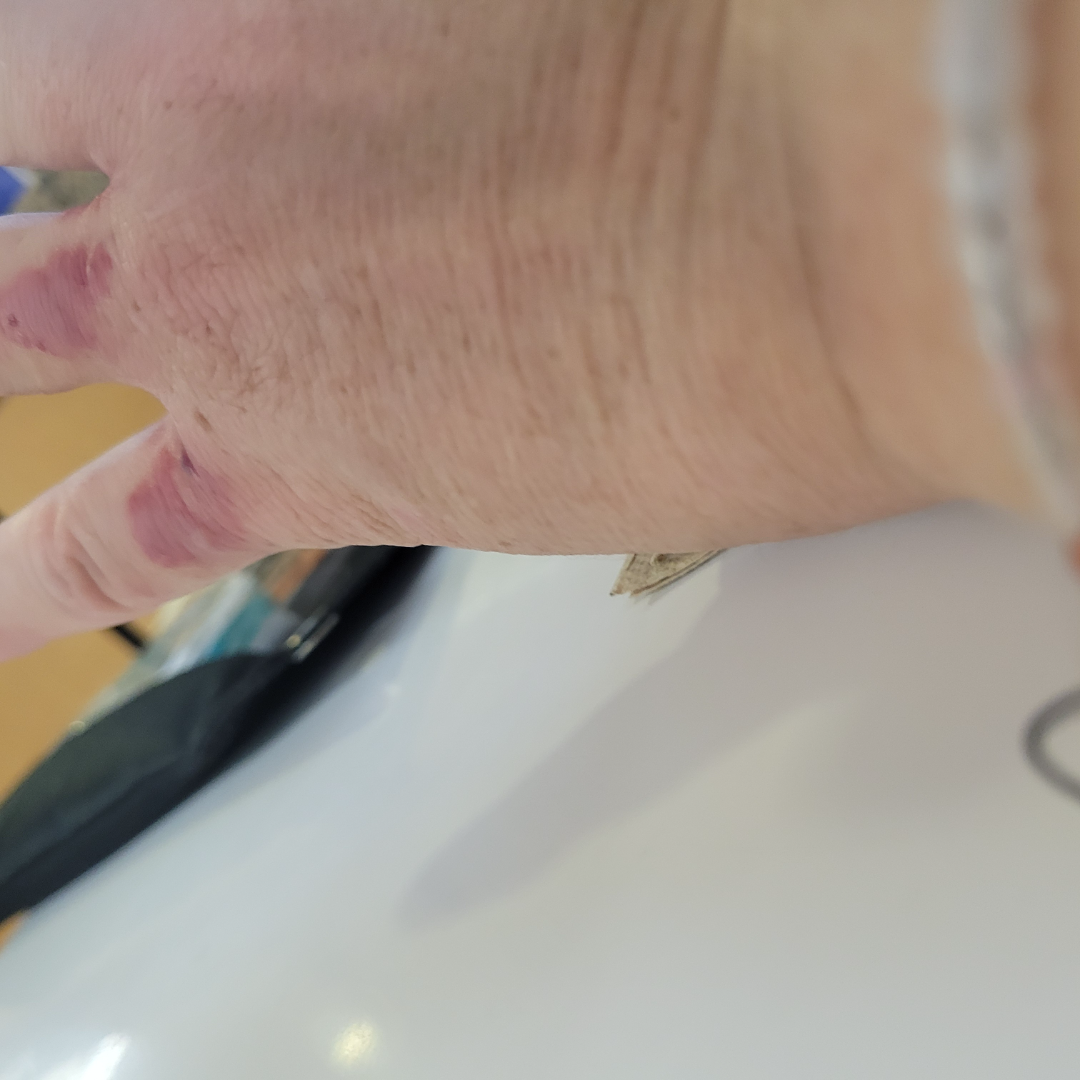The contributor reports the condition has been present for about one day. The contributor reports the lesion is raised or bumpy and fluid-filled. The patient described the issue as a rash. The photograph was taken at a distance. The affected area is the back of the hand and palm. The subject is 40–49, female. Tinea (0.33); Burn of skin (0.33); Allergic Contact Dermatitis (0.33).